A female subject aged approximately 60. A dermoscopic image of a skin lesion. The patient is Fitzpatrick skin type II.
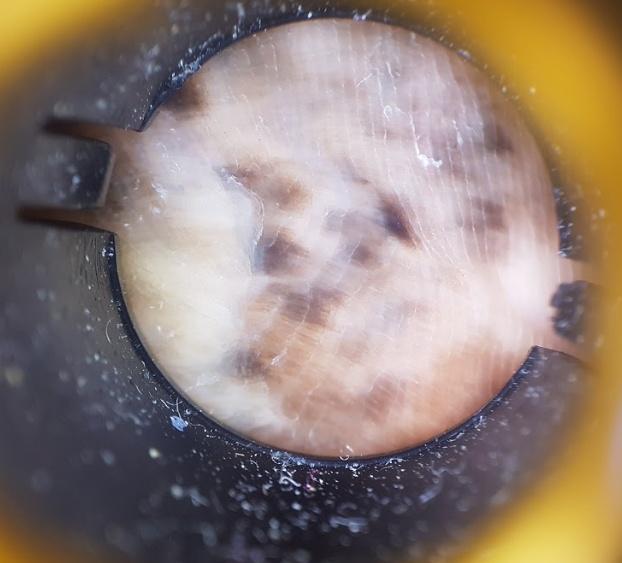The lesion is located on an acral site (palms or soles). Confirmed on histopathology as a melanoma.